A female subject aged approximately 60. The chart documents a prior melanoma. A clinical photograph showing a skin lesion in context.
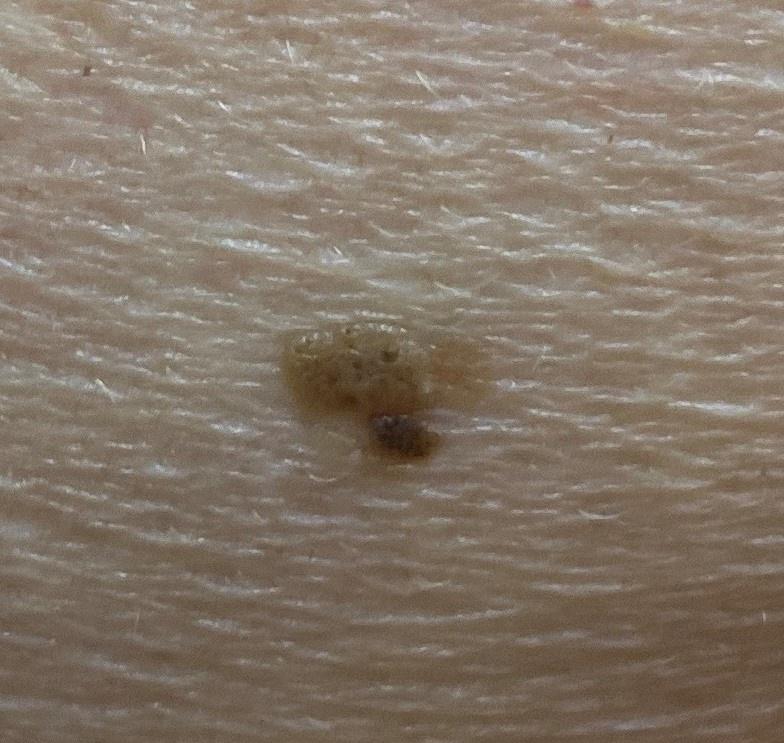Case:
- body site — the anterior trunk
- diagnosis — Seborrheic keratosis (clinical impression)